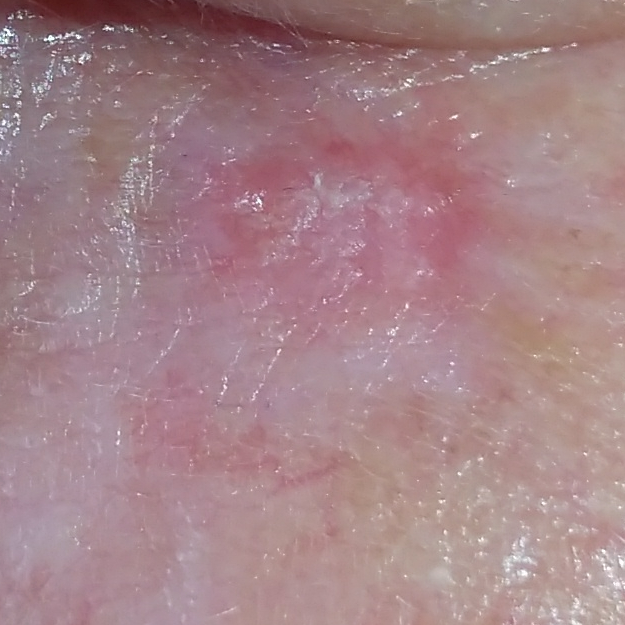Case summary: The chart records pesticide exposure, alcohol use, prior skin cancer (patient or family), no tobacco use, and no prior malignancy (patient or family). The patient is FST II. A female subject aged 60. A clinical photograph of a skin lesion. Located on the face. Measuring about 4 × 2 mm. Conclusion: Histopathologically confirmed as a lesion of indeterminate malignant potential — an actinic keratosis.